A female subject roughly 60 years of age. A contact-polarized dermoscopy image of a skin lesion.
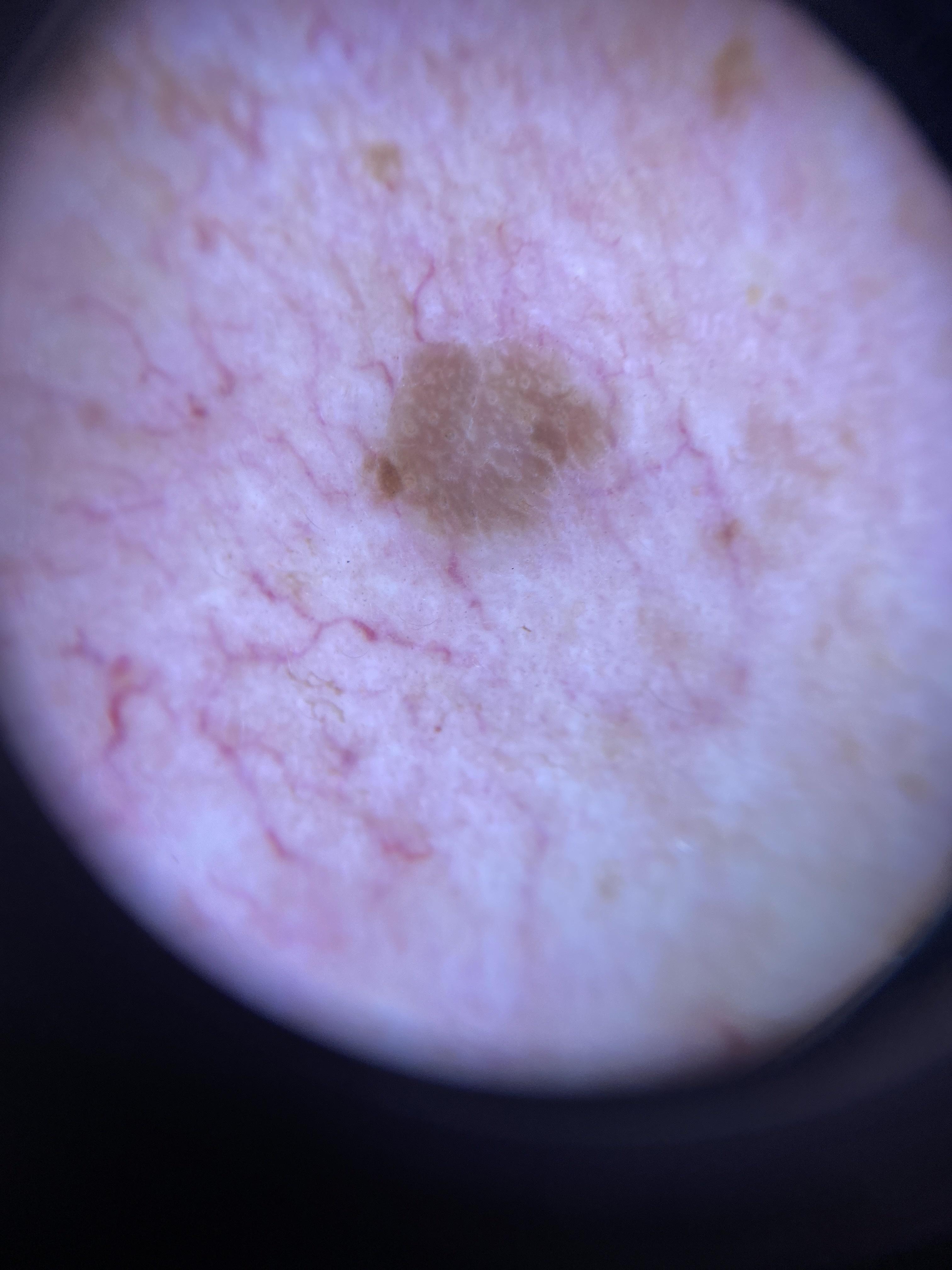The diagnostic impression was a seborrheic keratosis.